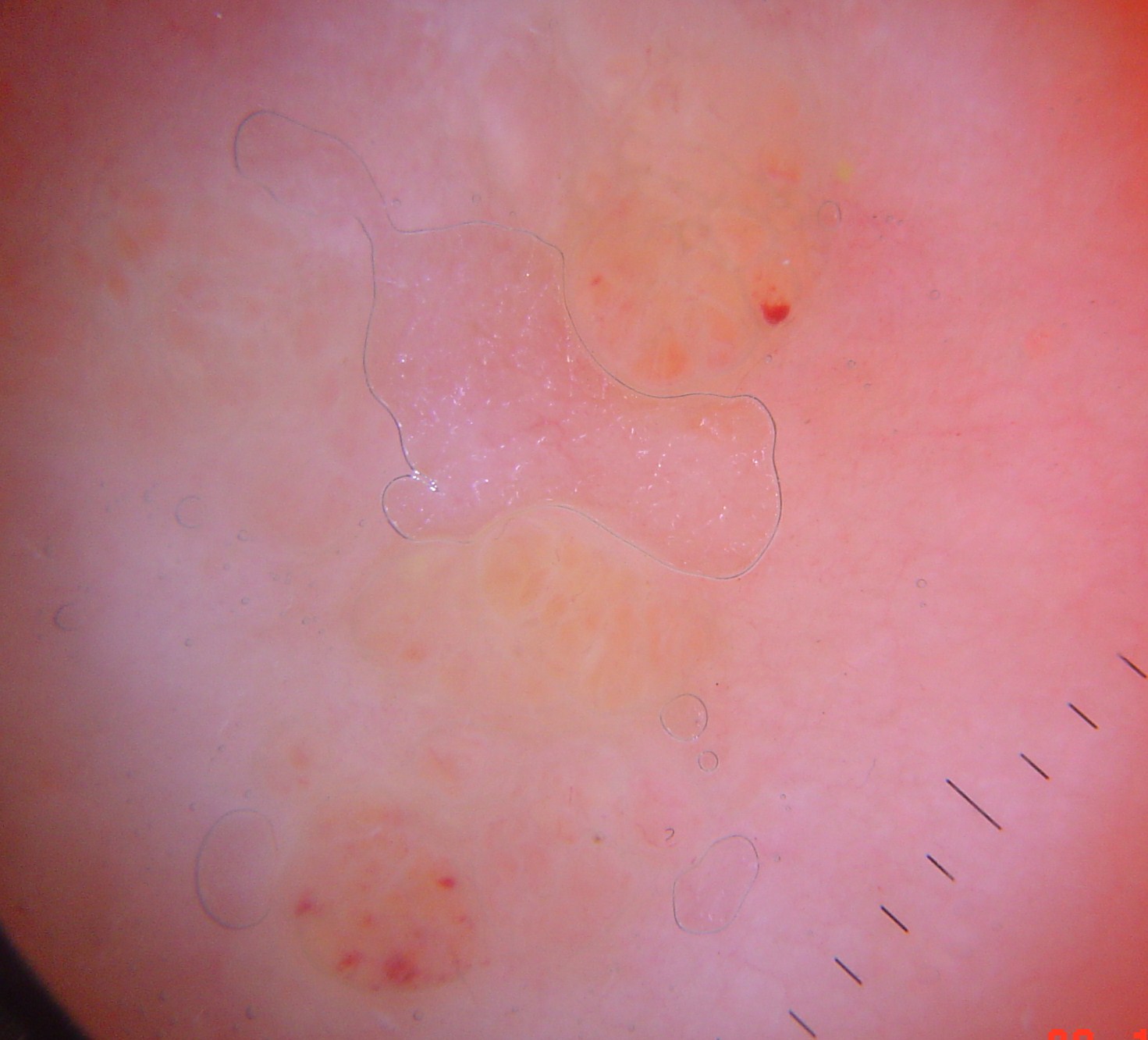A skin lesion imaged with a dermatoscope. Labeled as a vascular lesion — a lymphangioma.